A dermoscopy image of a single skin lesion.
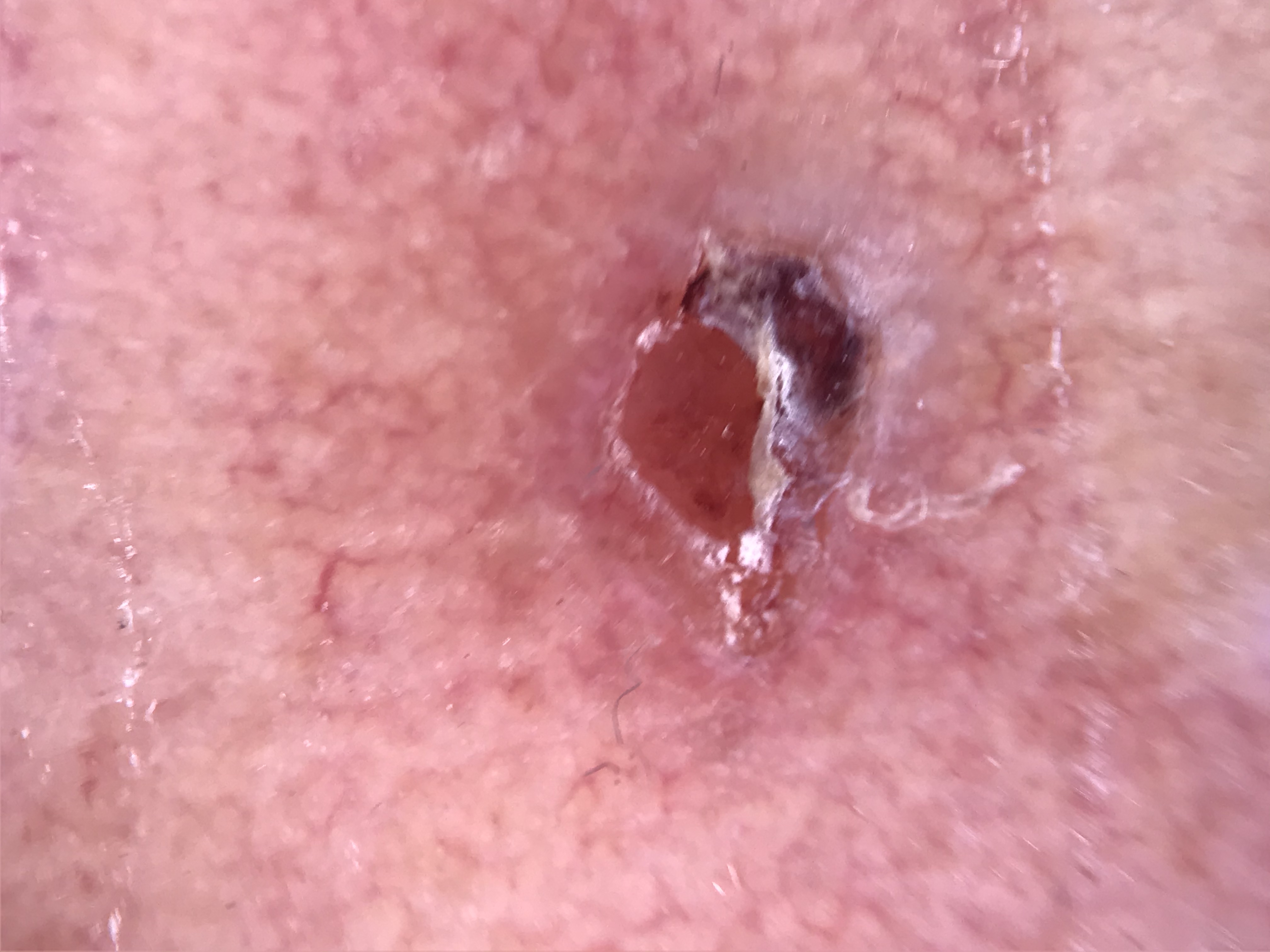Q: What did the workup show?
A: squamous cell carcinoma (biopsy-proven)